Close-up view. Female contributor, age 50–59. The back of the torso is involved: 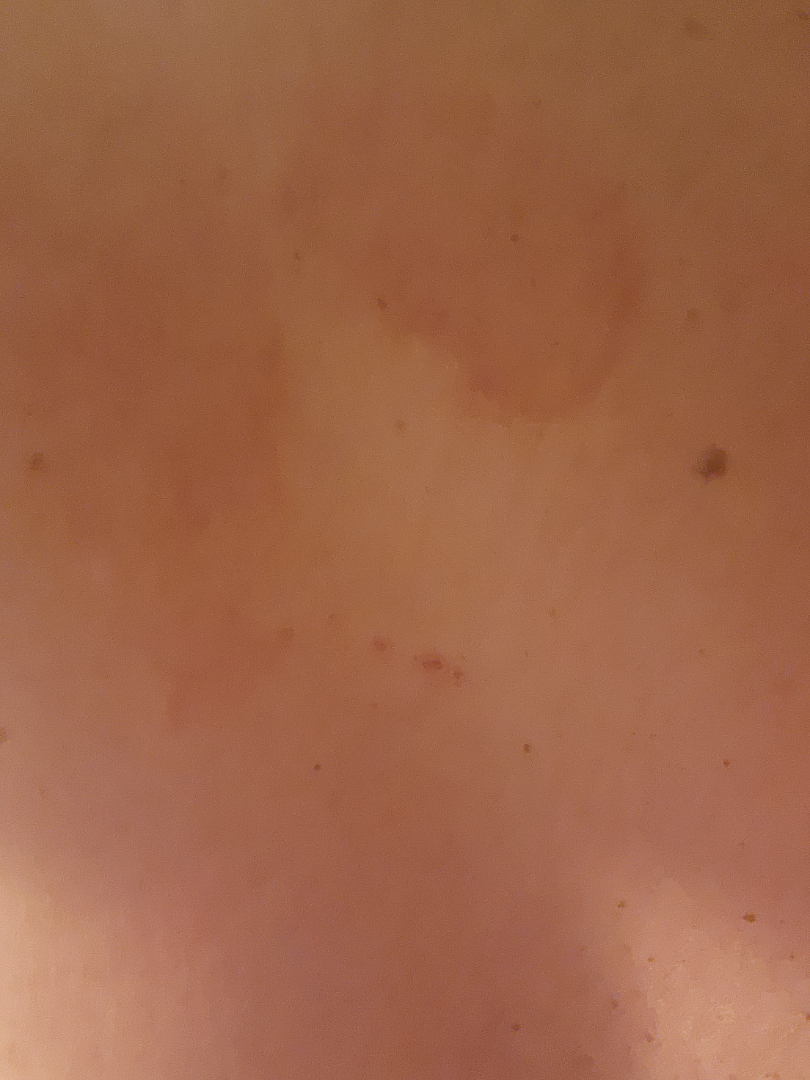The image was not sufficient for the reviewer to characterize the skin condition. The lesion is associated with bothersome appearance and pain. Present for one to four weeks. Skin tone: non-clinician graders estimated 3 on the Monk Skin Tone. The patient notes the lesion is flat and rough or flaky. The patient also reports joint pain and fatigue.